A dermoscopic view of a skin lesion · a female patient in their mid-50s:
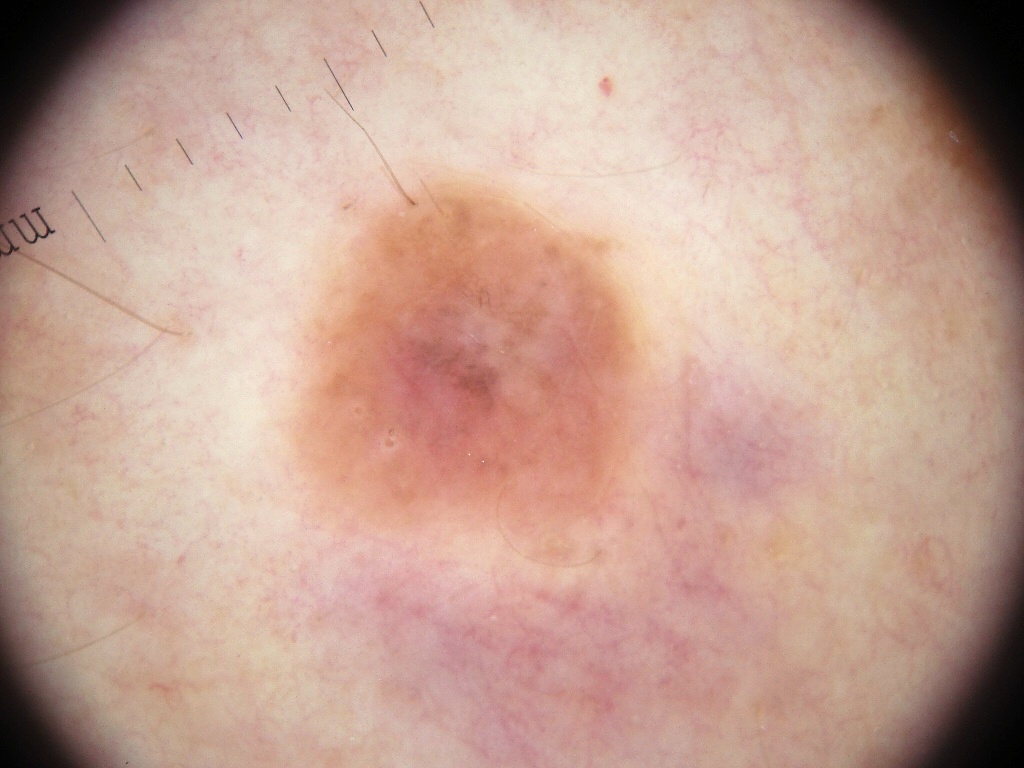| feature | finding |
|---|---|
| lesion extent | ~18% of the field |
| dermoscopic pattern | pigment network |
| lesion bbox | x1=267, y1=162, x2=677, y2=591 |
| impression | a melanocytic nevus, a benign lesion |